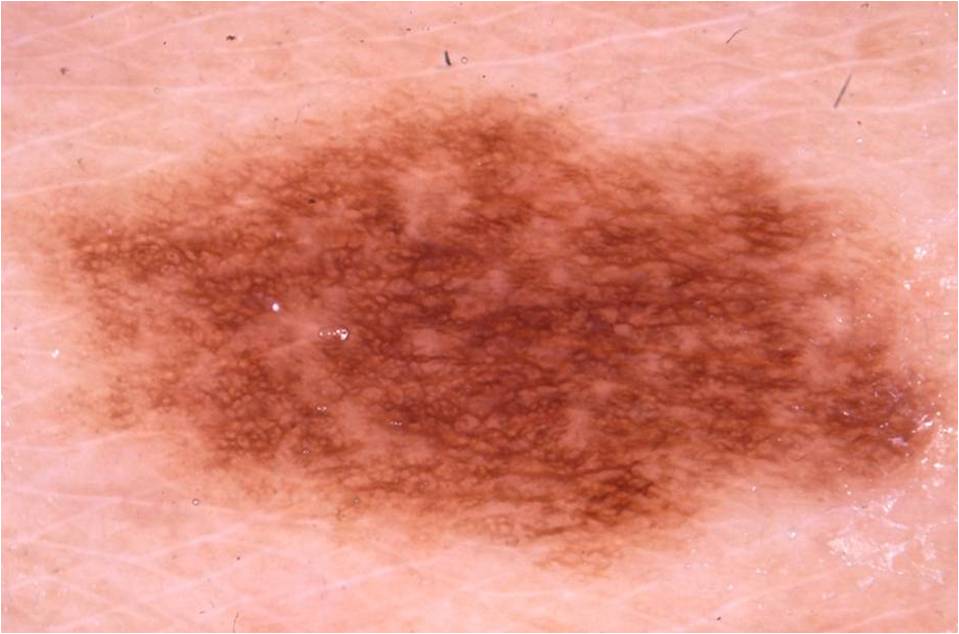<lesion>
<image>
  <modality>dermoscopy</modality>
</image>
<lesion_location>
  <bbox_xyxy>10, 78, 954, 574</bbox_xyxy>
</lesion_location>
<diagnosis>
  <name>melanocytic nevus</name>
  <malignancy>benign</malignancy>
  <lineage>melanocytic</lineage>
  <provenance>clinical</provenance>
</diagnosis>
</lesion>